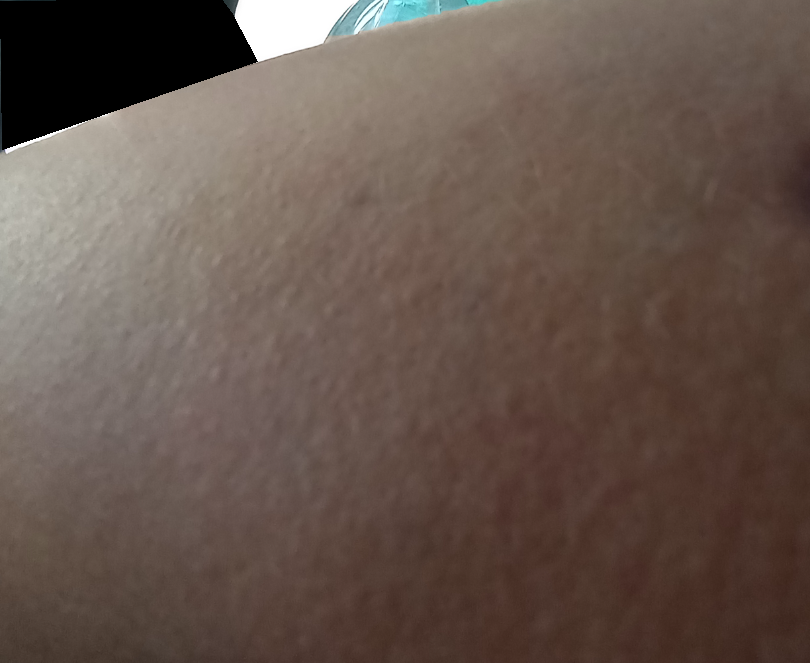Findings: The reviewer was unable to grade this case for skin condition. Background: The patient indicates the lesion is raised or bumpy. The photograph is a close-up of the affected area. The condition has been present for less than one week. The affected area is the arm. The patient described the issue as a rash. The lesion is associated with itching and bothersome appearance.